Female subject, age 18–29. The affected area is the top or side of the foot. An image taken at a distance:
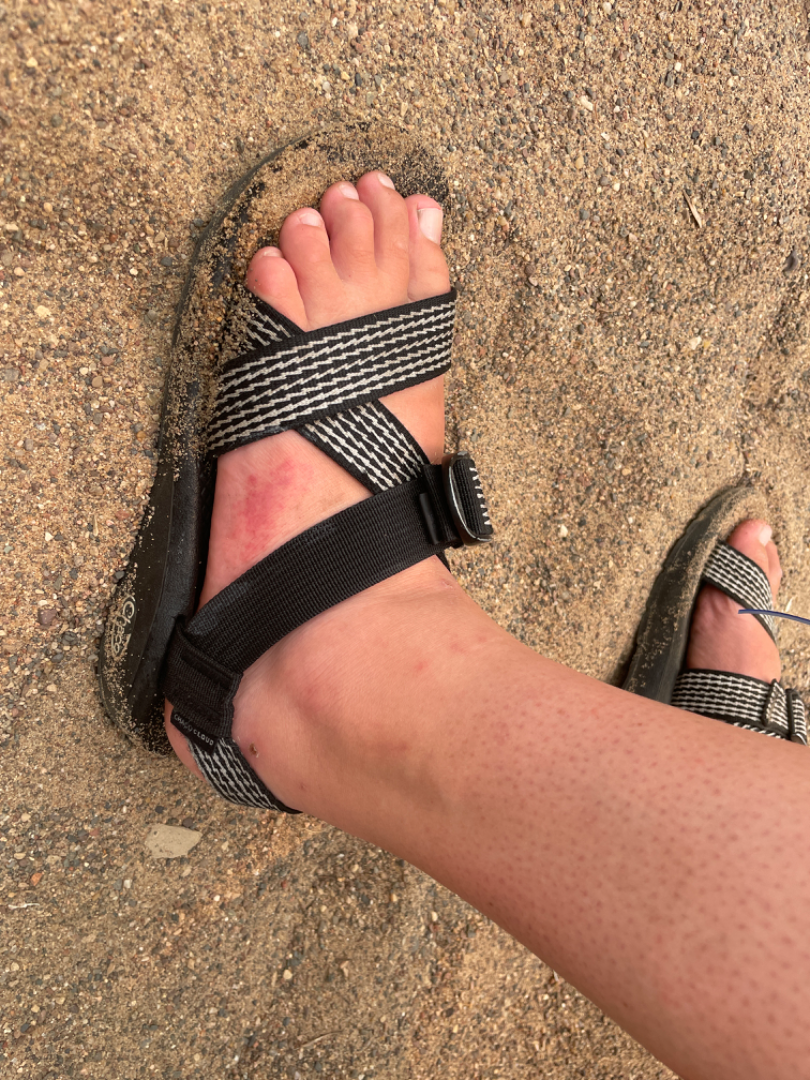  assessment: unable to determine